A dermoscopic image of a skin lesion.
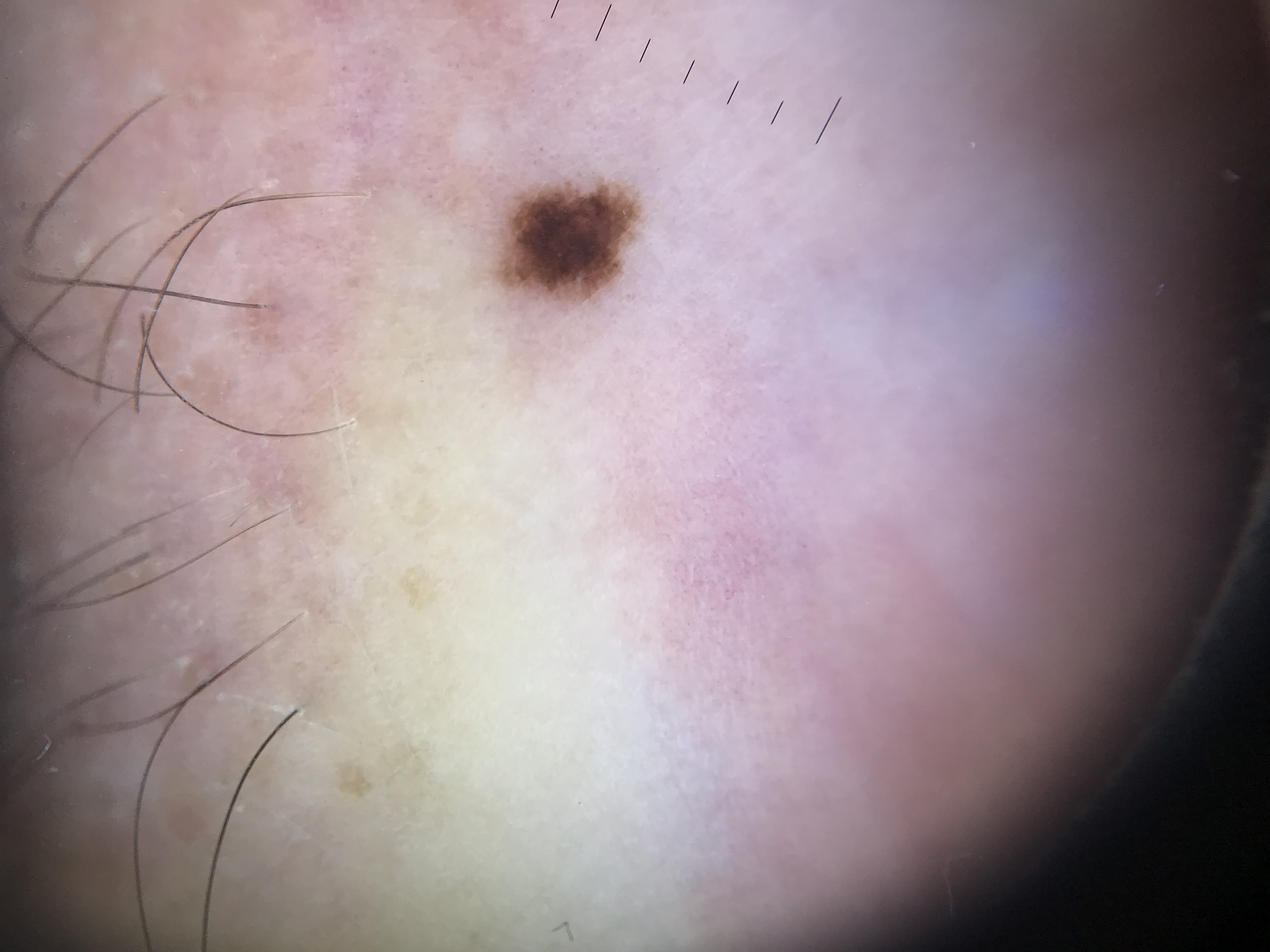The architecture is that of a banal lesion. Classified as a junctional nevus.